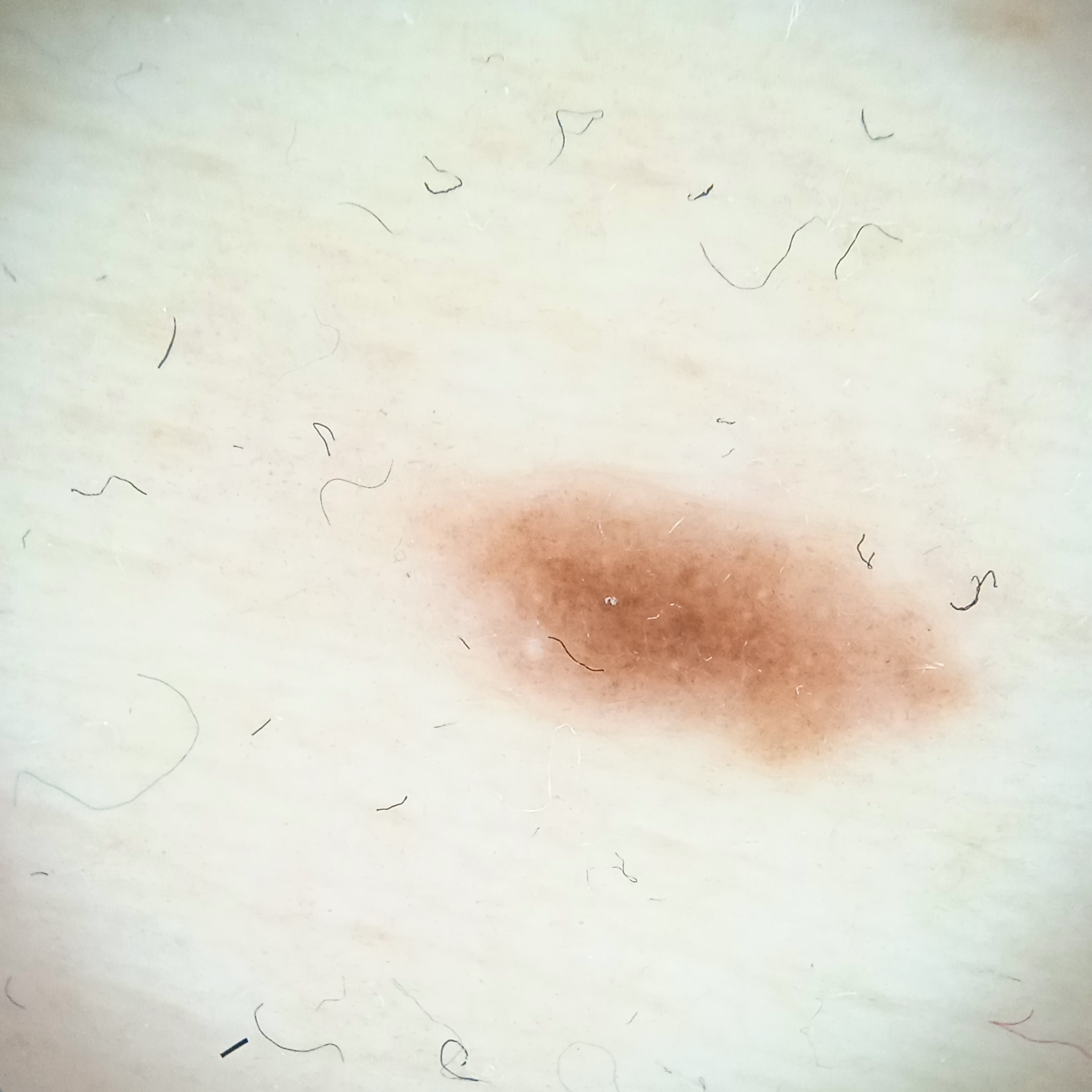Assessment: Dermatologist review favored a melanocytic nevus.